The contributor is 18–29, male. Located on the leg. The patient reports the lesion is flat and raised or bumpy. The condition has been present for about one day. Fitzpatrick skin type III; lay reviewers estimated Monk Skin Tone 1 or 2. The patient reports enlargement and itching. The photograph was taken at an angle — 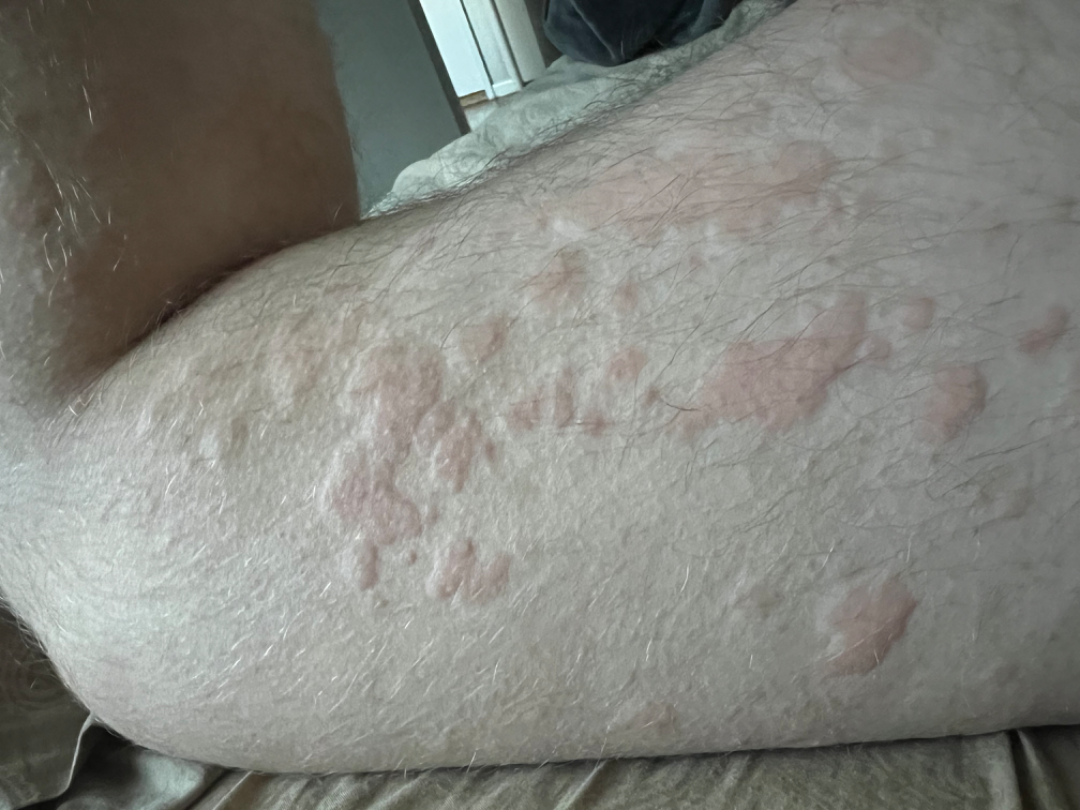On photographic review, most consistent with Urticaria.